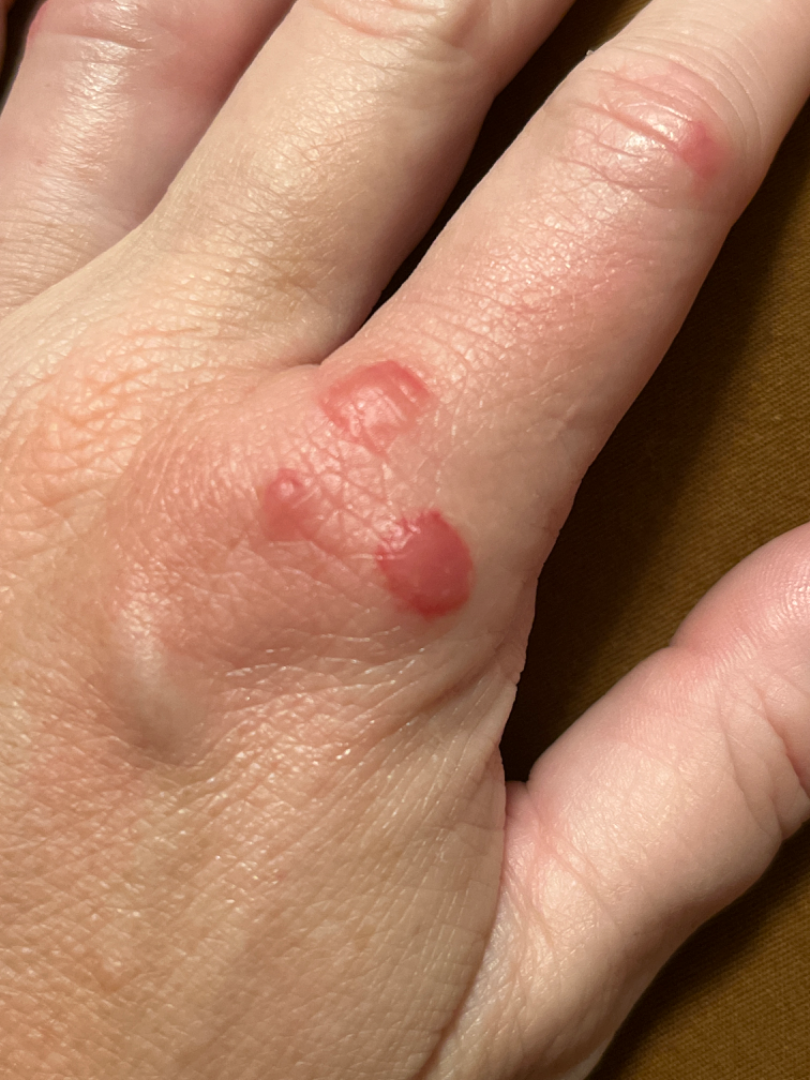The skin findings could not be characterized from the image.